A skin lesion imaged with a dermatoscope.
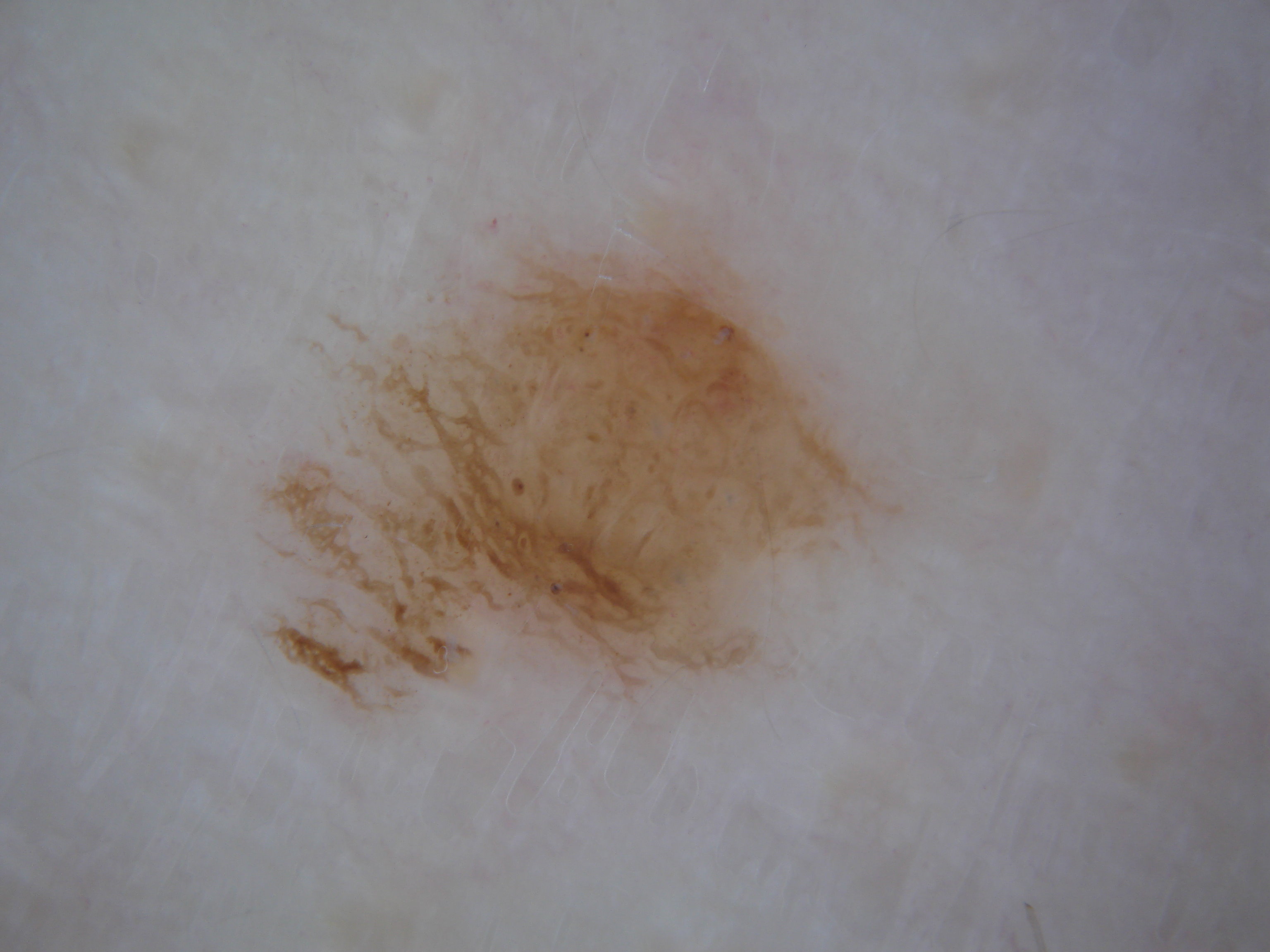As (left, top, right, bottom), the lesion is bounded by 216 180 968 755. Dermoscopy demonstrates globules and pigment network. Clinically diagnosed as a melanocytic nevus, a benign lesion.